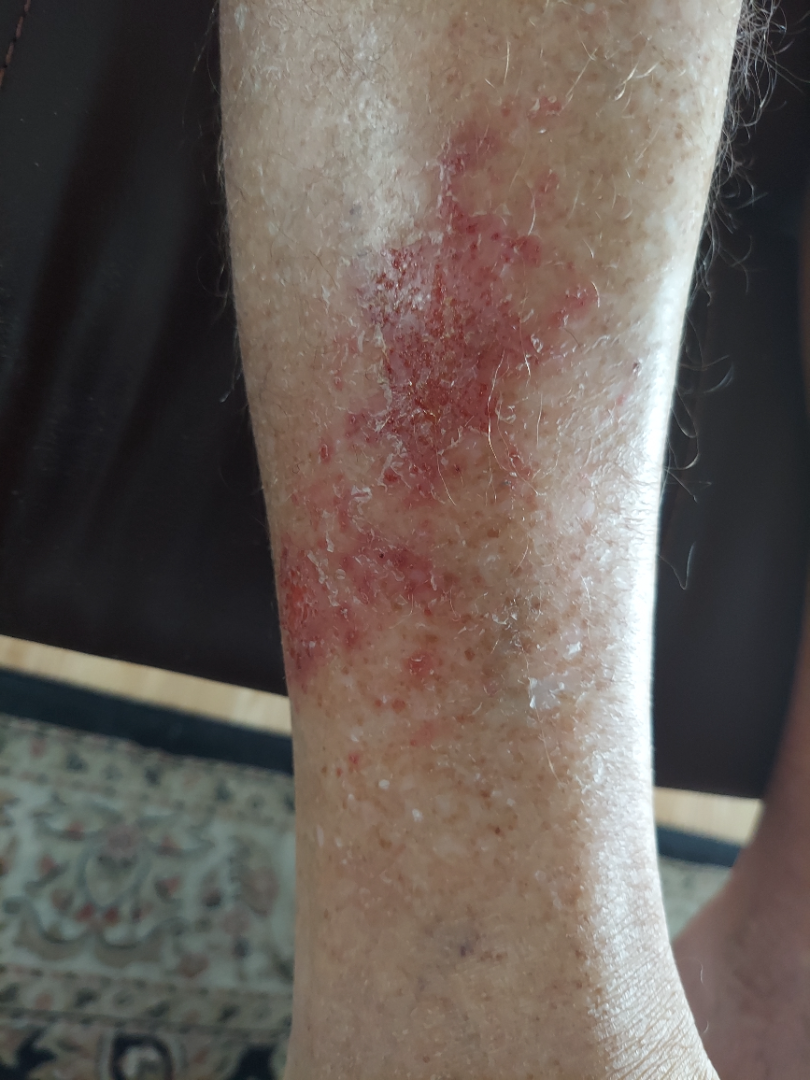Close-up view. The lesion involves the leg. The reviewing clinician's impression was: most likely Infected eczema; possibly Psoriasis.